The patient is a female in their mid-60s. A dermoscopic view of a skin lesion — 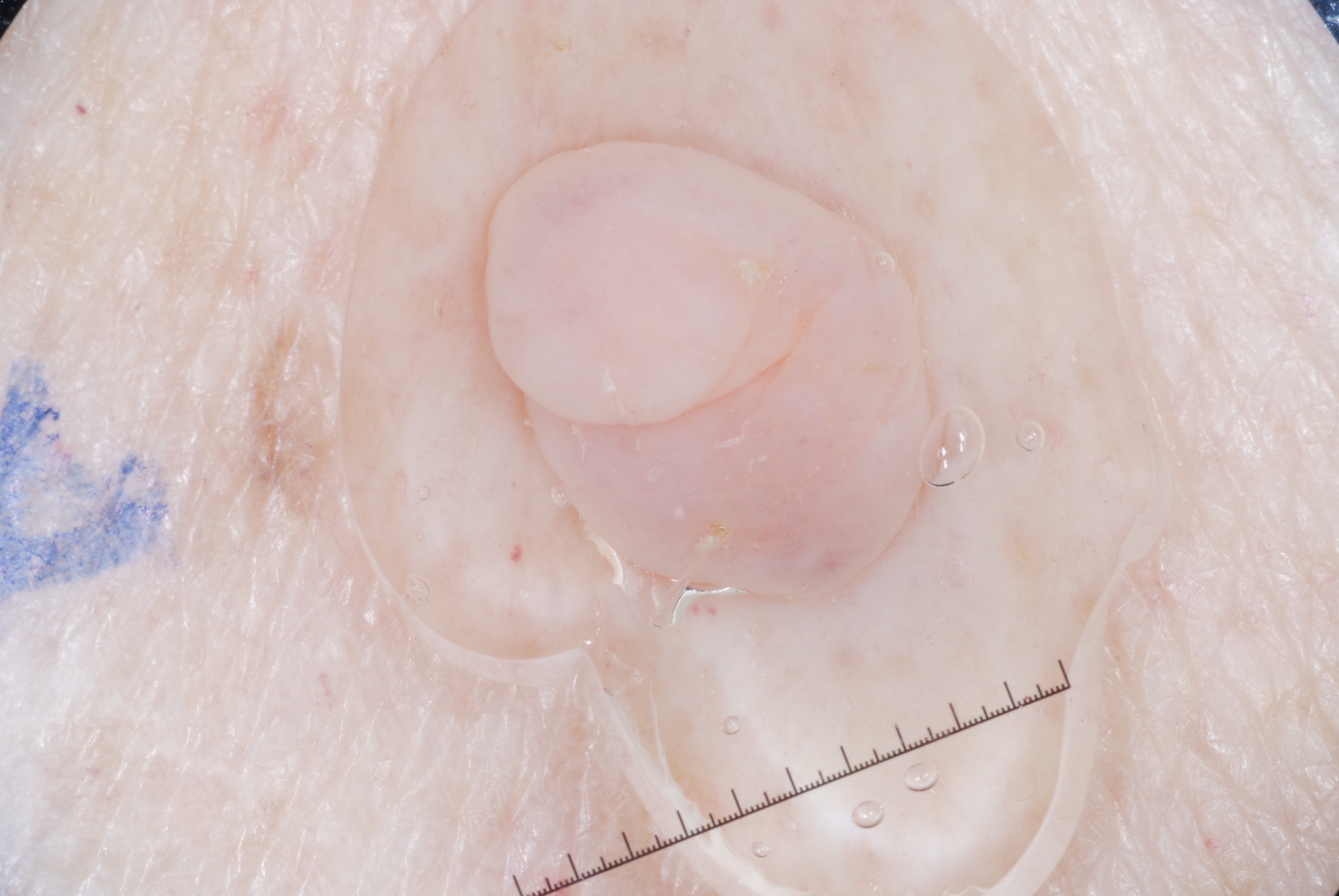{"dermoscopic_features": {"present": [], "absent": ["pigment network", "streaks", "milia-like cysts", "negative network"]}, "lesion_location": {"bbox_xyxy": [463, 124, 955, 649]}, "lesion_extent": "moderate", "diagnosis": {"name": "melanocytic nevus", "malignancy": "benign", "lineage": "melanocytic", "provenance": "clinical"}}